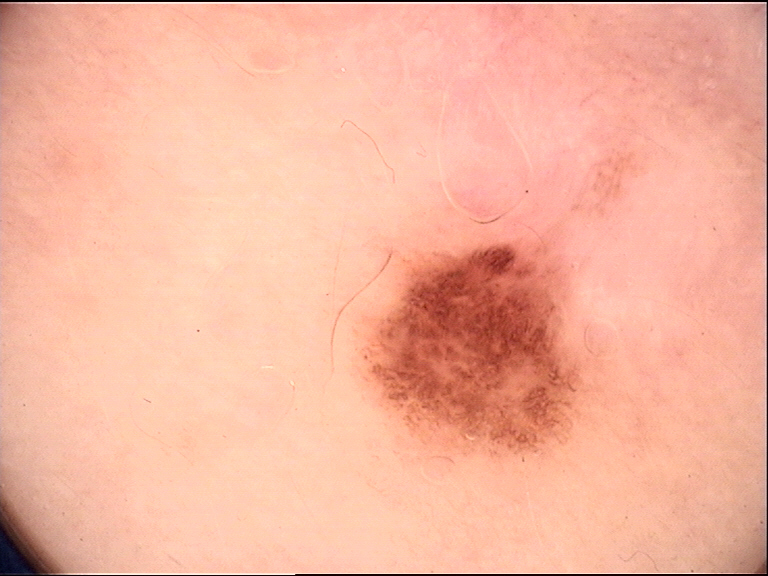The diagnostic label was a benign lesion — a dysplastic junctional nevus.